The subject is a female aged 18–29. The arm, leg, back of the torso, front of the torso and head or neck are involved. Close-up view: 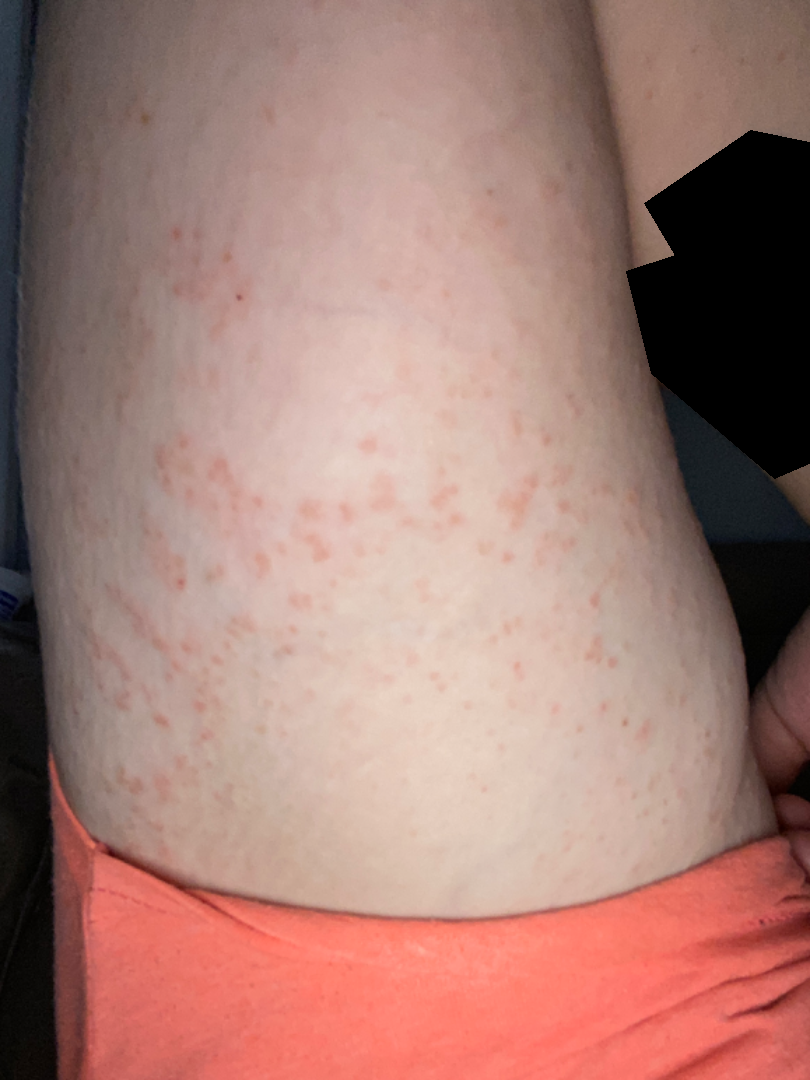Q: What is the dermatologist's impression?
A: reviewed remotely by one dermatologist: most likely Contact dermatitis, NOS; also raised was Eczema; less likely is Keratosis pilaris